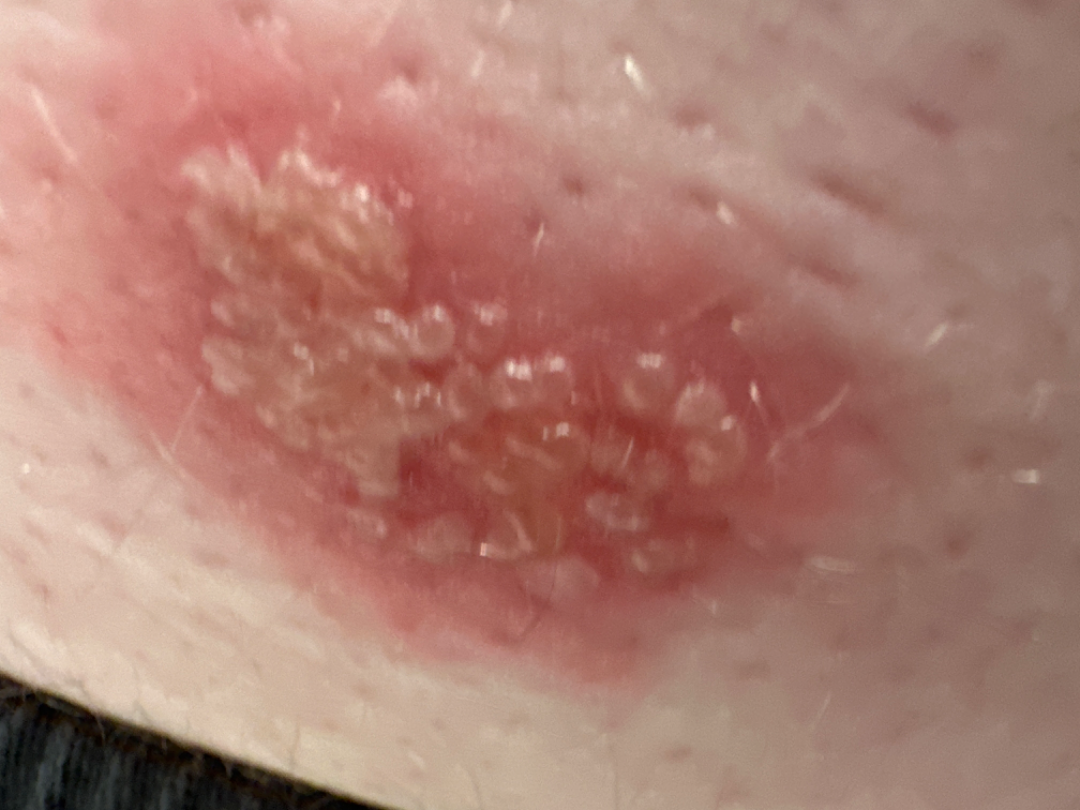Findings: The leading consideration is Herpes Simplex; less likely is Lymphangioma; less probable is Herpes Zoster.